The arm is involved · an image taken at an angle · reported lesion symptoms include itching · the patient described the issue as a rash · the condition has been present for less than one week: 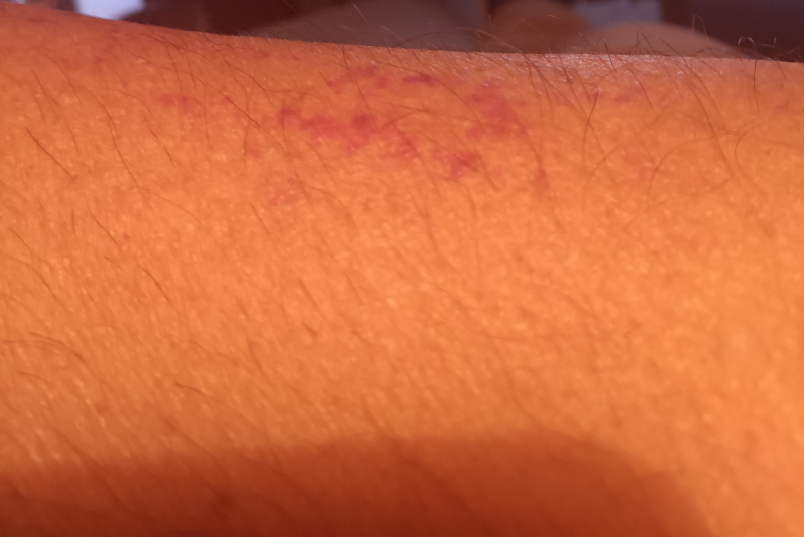The reviewer was unable to grade this case for skin condition.